The patient is 18–29, female; the lesion is described as rough or flaky and flat; a close-up photograph; reported duration is three to twelve months; associated systemic symptoms include mouth sores and fatigue; located on the leg — 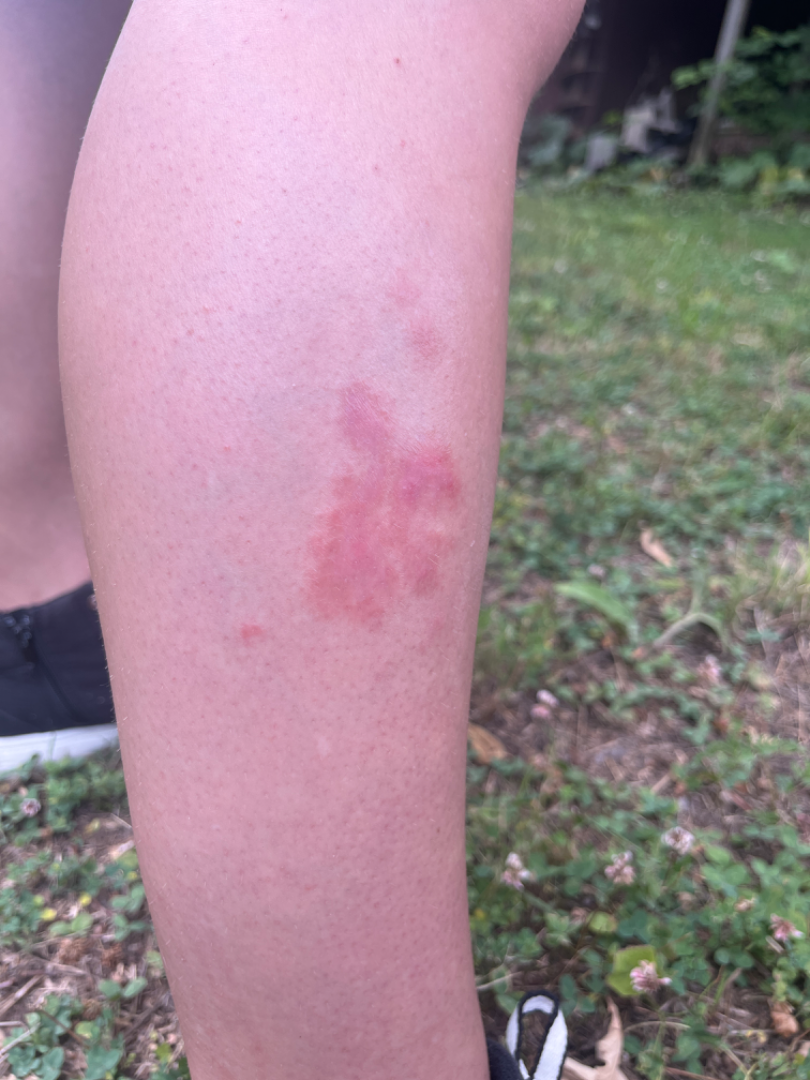Q: What conditions are considered?
A: the favored diagnosis is Allergic Contact Dermatitis